A dermoscopic photograph of a skin lesion.
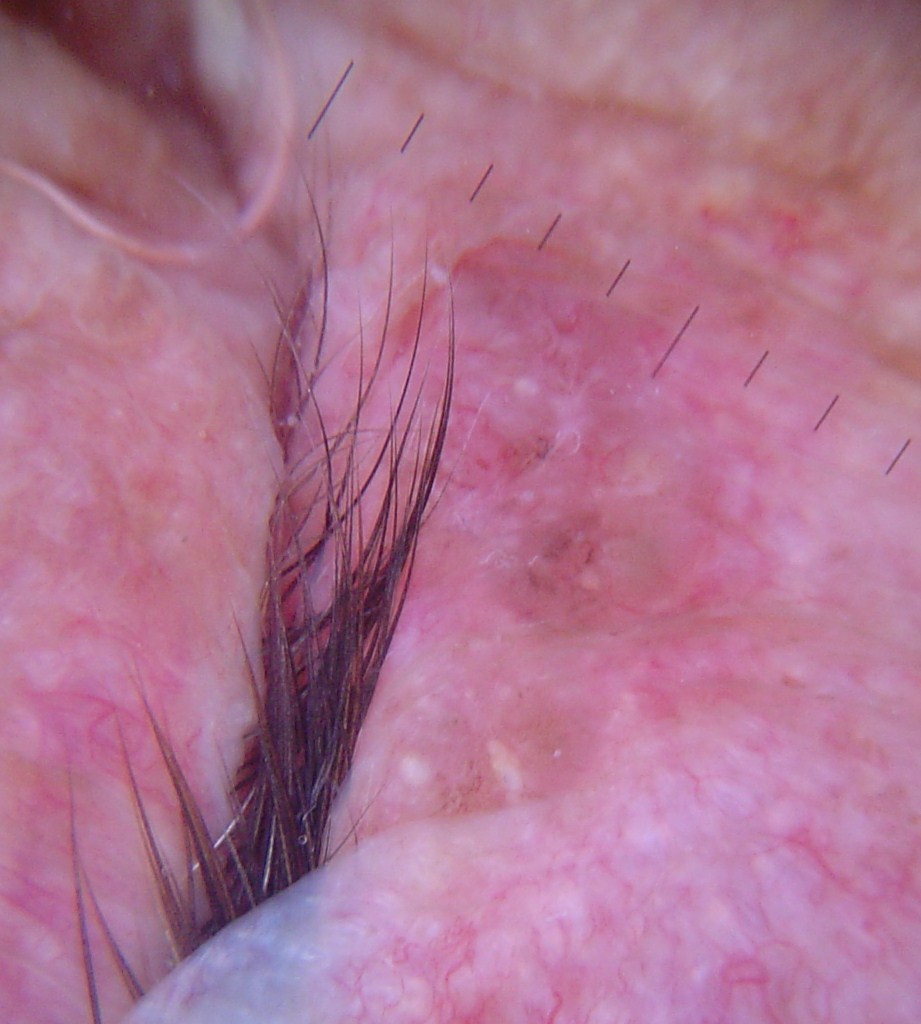<case>
  <diagnosis>
    <name>basal cell carcinoma</name>
    <code>bcc</code>
    <malignancy>malignant</malignancy>
    <super_class>non-melanocytic</super_class>
    <confirmation>histopathology</confirmation>
  </diagnosis>
</case>